The chart notes tobacco use, alcohol use, prior skin cancer (patient or family), prior malignancy (patient or family), and no pesticide exposure · the patient was assessed as skin type II:
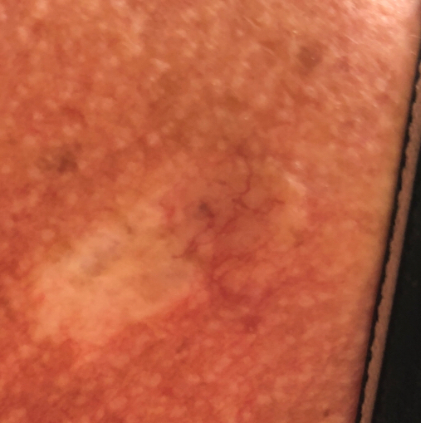| key | value |
|---|---|
| lesion size | 20x16 mm |
| patient-reported symptoms | elevation |
| diagnostic label | basal cell carcinoma (biopsy-proven) |